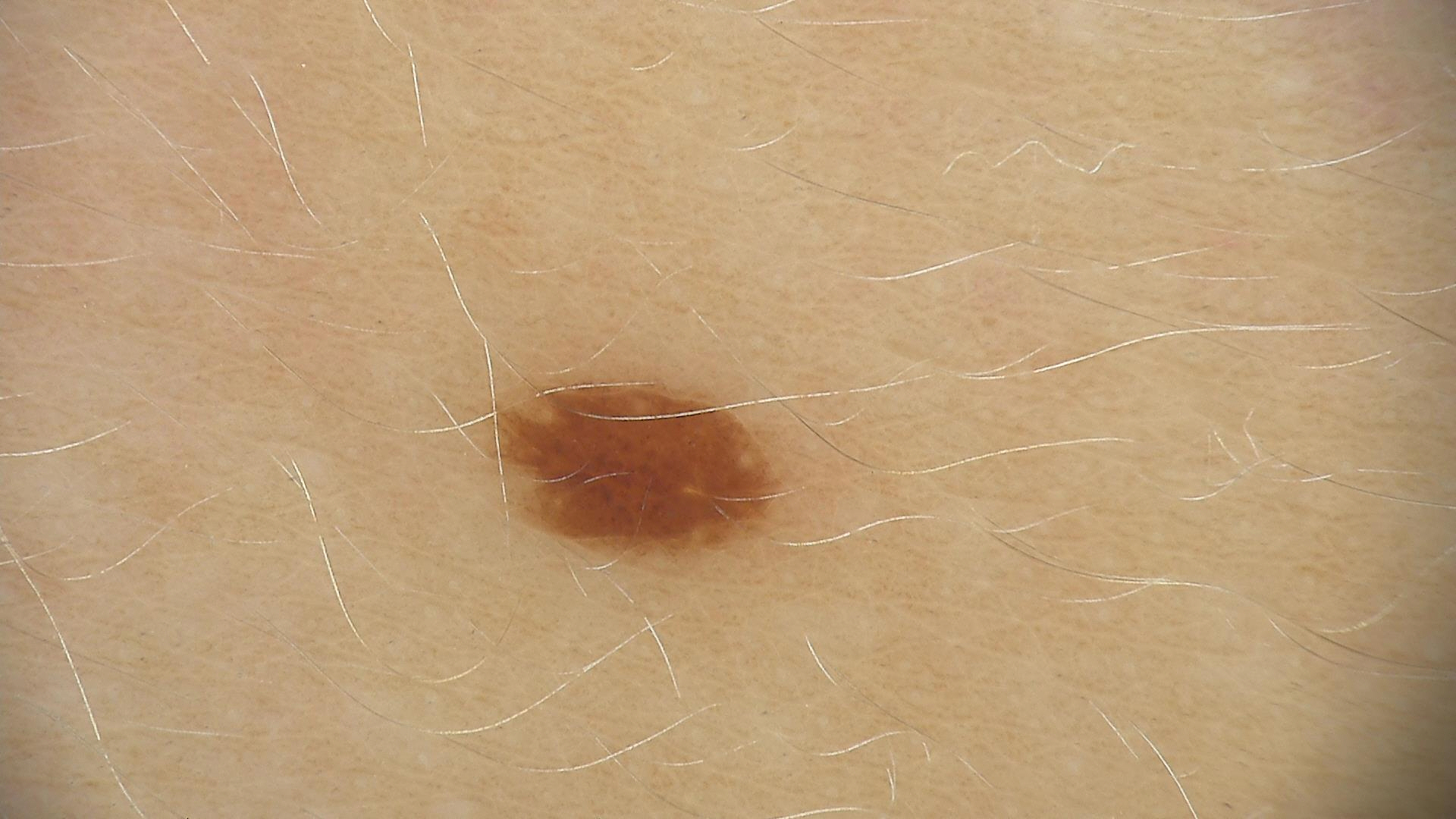<dermoscopy>
  <image>dermoscopy</image>
  <diagnosis>
    <name>dysplastic junctional nevus</name>
    <code>jd</code>
    <malignancy>benign</malignancy>
    <super_class>melanocytic</super_class>
    <confirmation>expert consensus</confirmation>
  </diagnosis>
</dermoscopy>